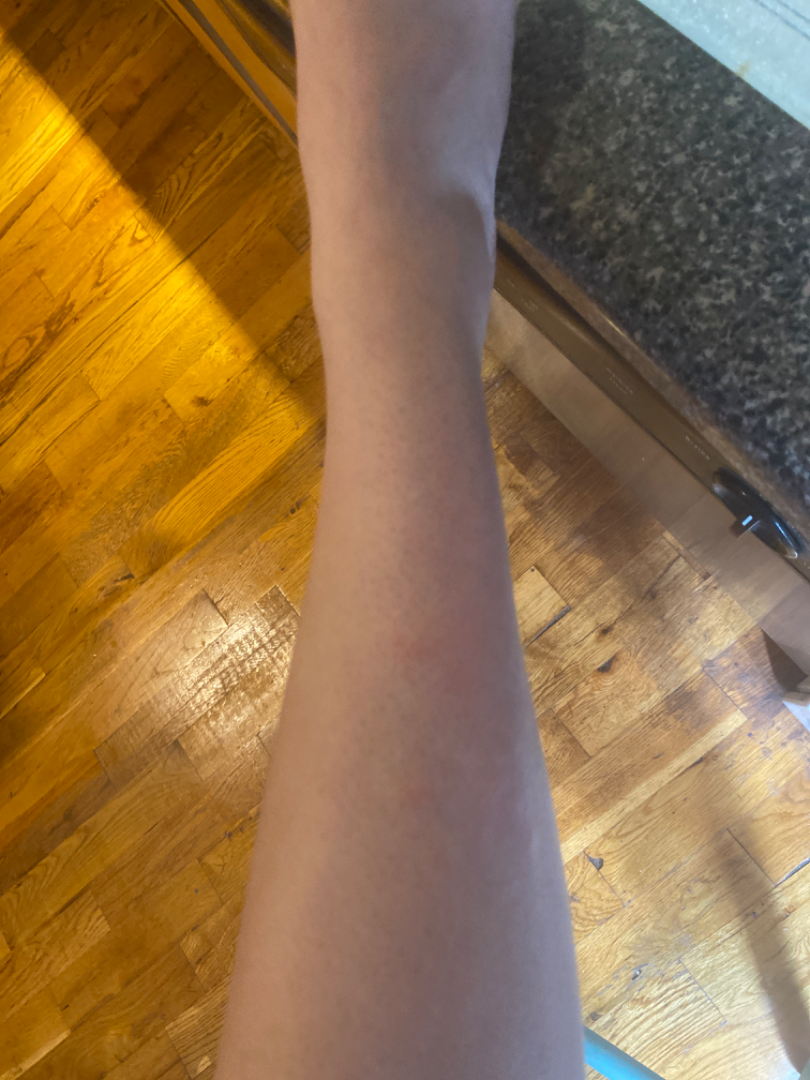assessment = ungradable on photographic review.